The subject is a male roughly 45 years of age, a dermoscopic close-up of a skin lesion: 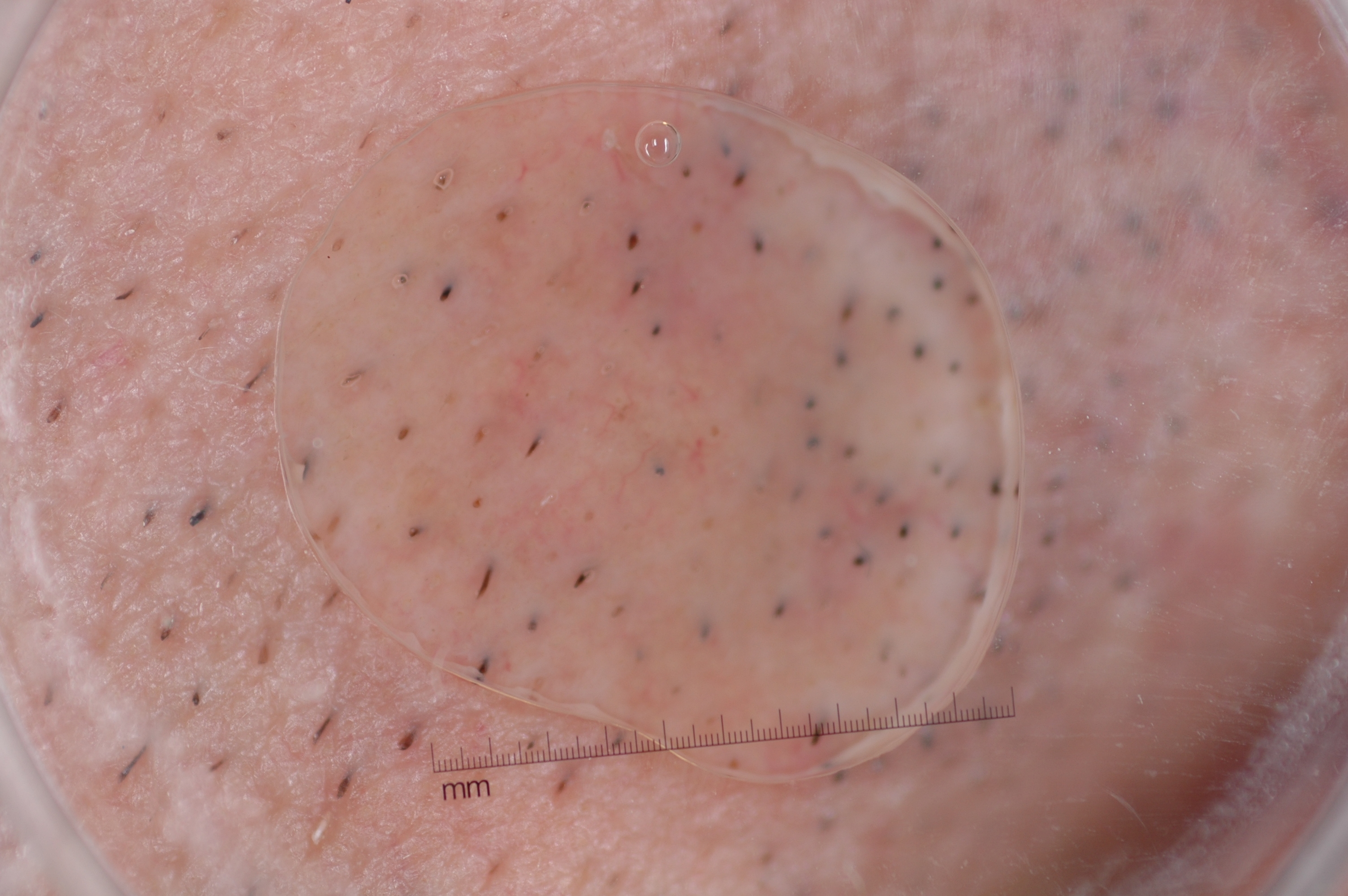The lesion's extent is left=399, top=122, right=947, bottom=749.
Dermoscopic review identifies no milia-like cysts, negative network, pigment network, or streaks.
Consistent with a melanocytic nevus, a benign lesion.